Acquired for a research image collection, with no referral diagnosis · a male patient 65 years old.
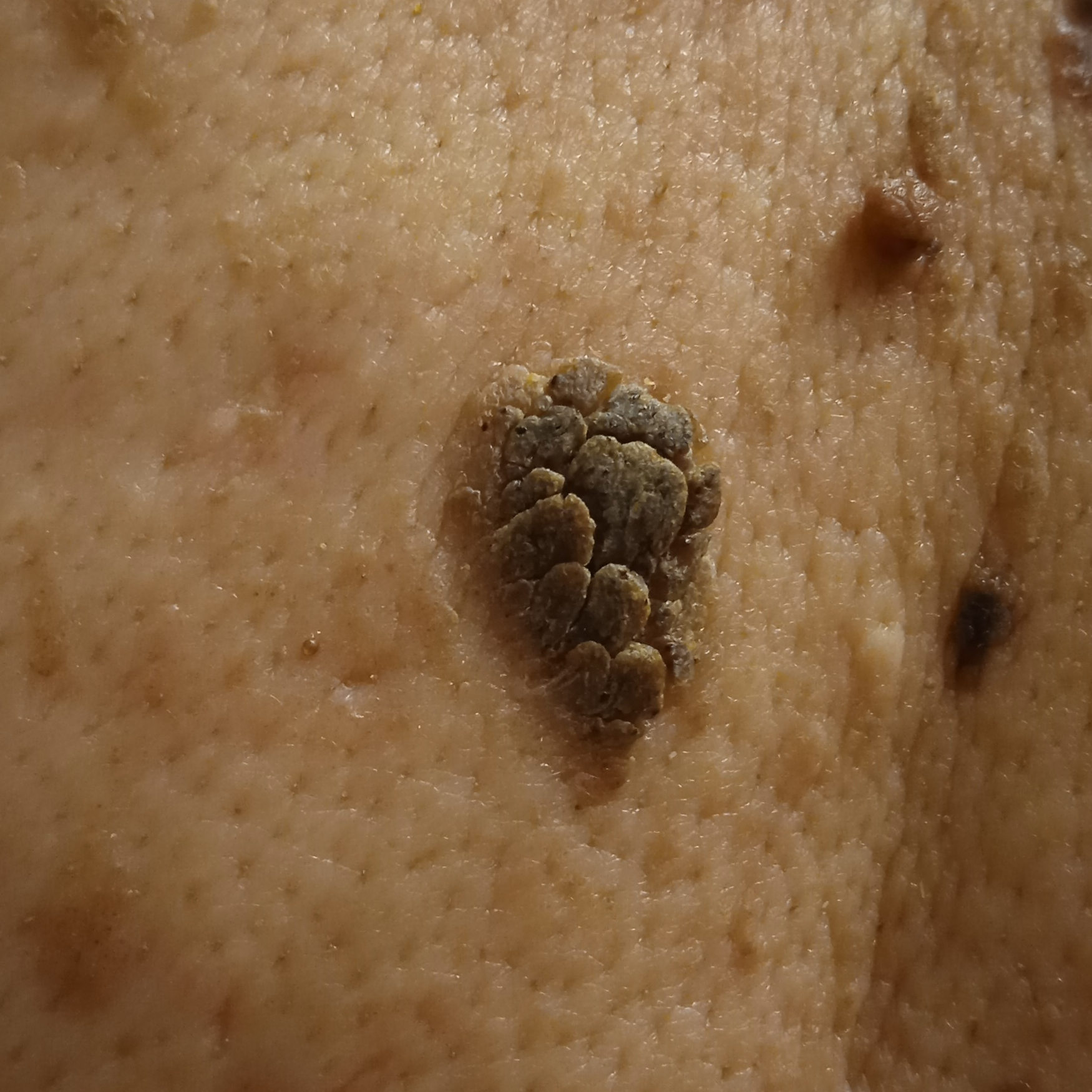<skin_lesion>
  <lesion_location>the back</lesion_location>
  <lesion_size>
    <diameter_mm>18.8</diameter_mm>
  </lesion_size>
  <diagnosis>
    <name>seborrheic keratosis</name>
    <malignancy>benign</malignancy>
  </diagnosis>
</skin_lesion>